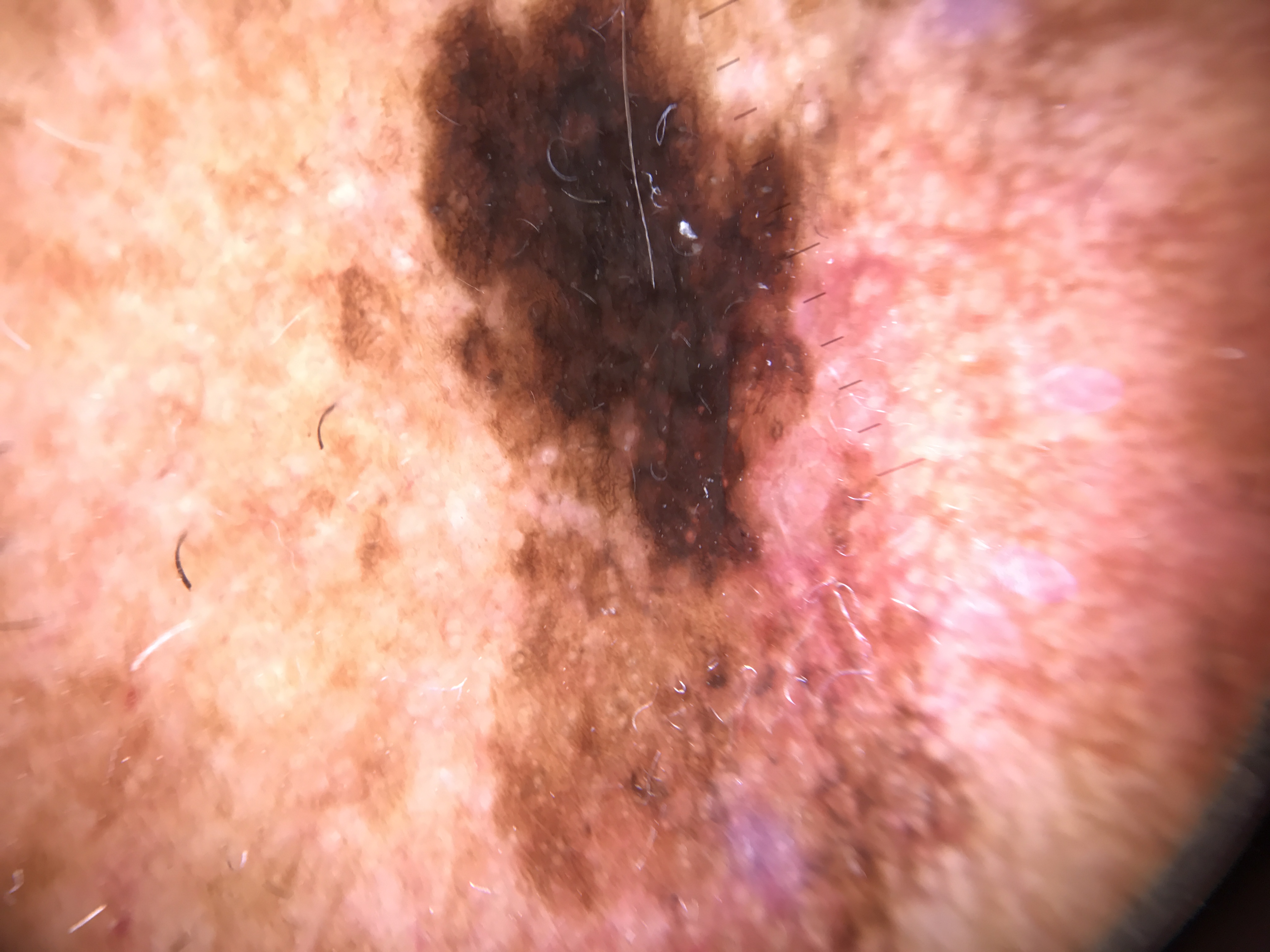| key | value |
|---|---|
| diagnosis | lentigo maligna (biopsy-proven) |